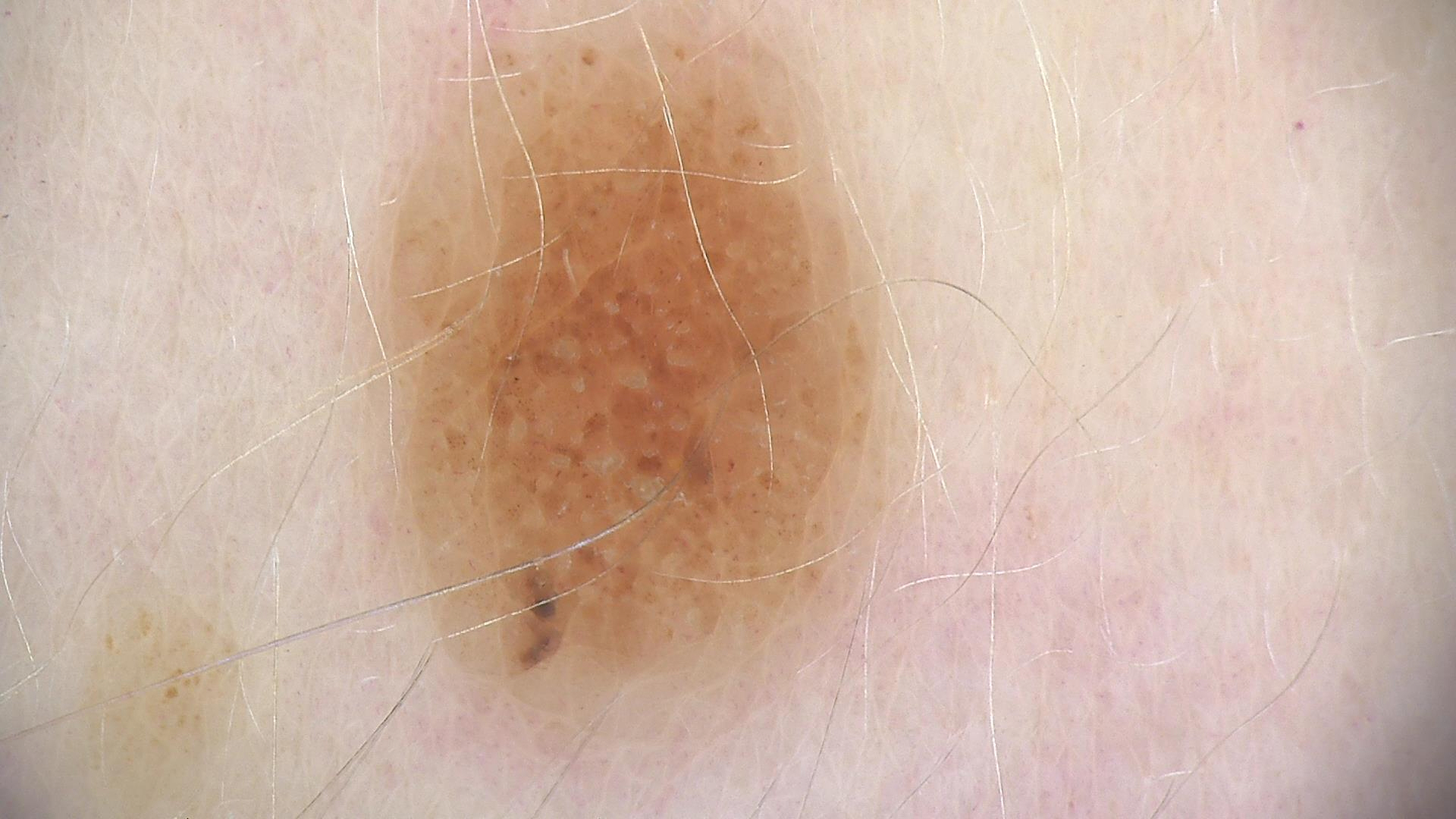A dermatoscopic image of a skin lesion.
The architecture is that of a banal lesion.
The diagnostic label was a compound nevus.